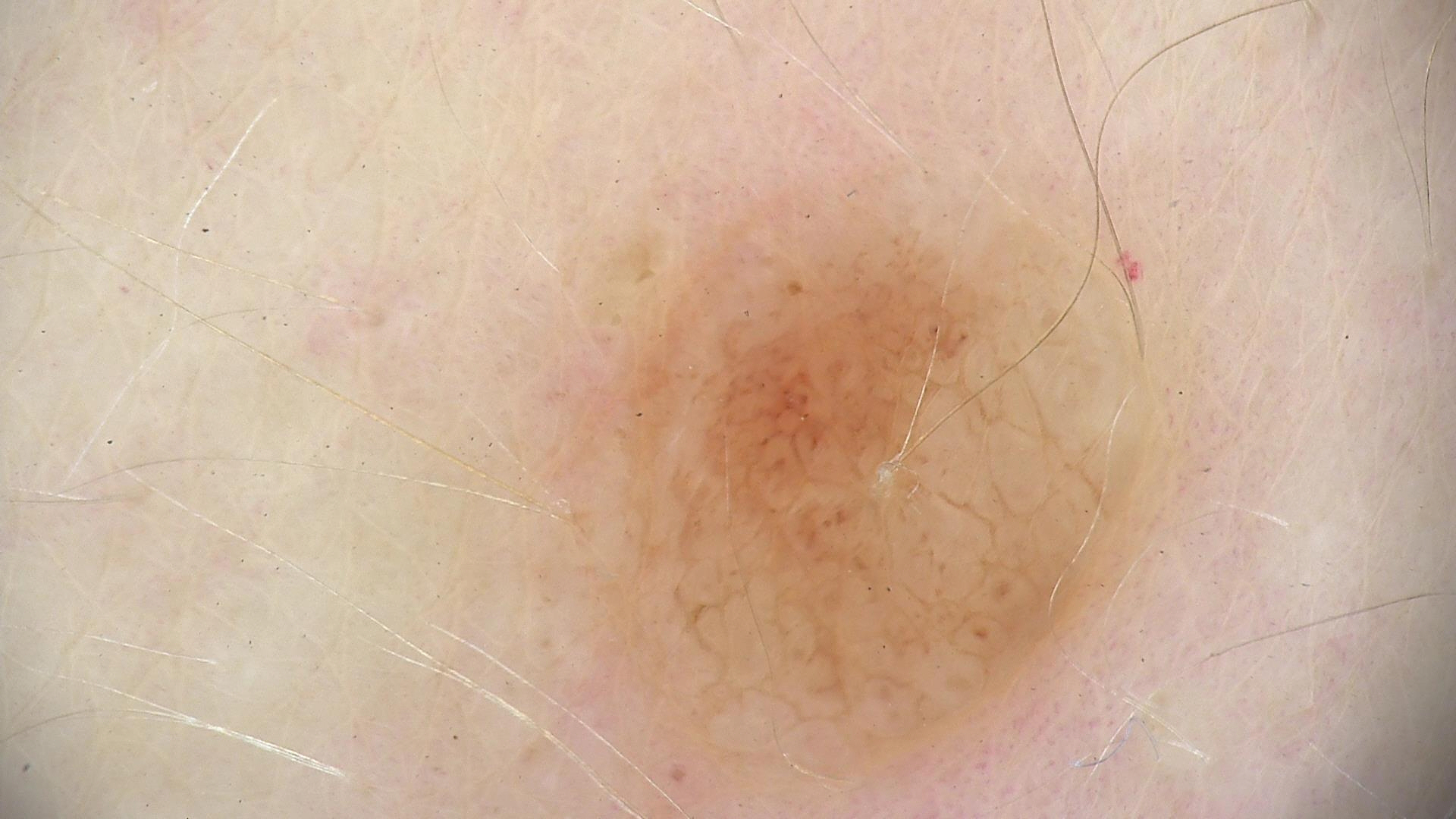A skin lesion imaged with a dermatoscope.
The morphology is that of a banal lesion.
Diagnosed as a dermal nevus.